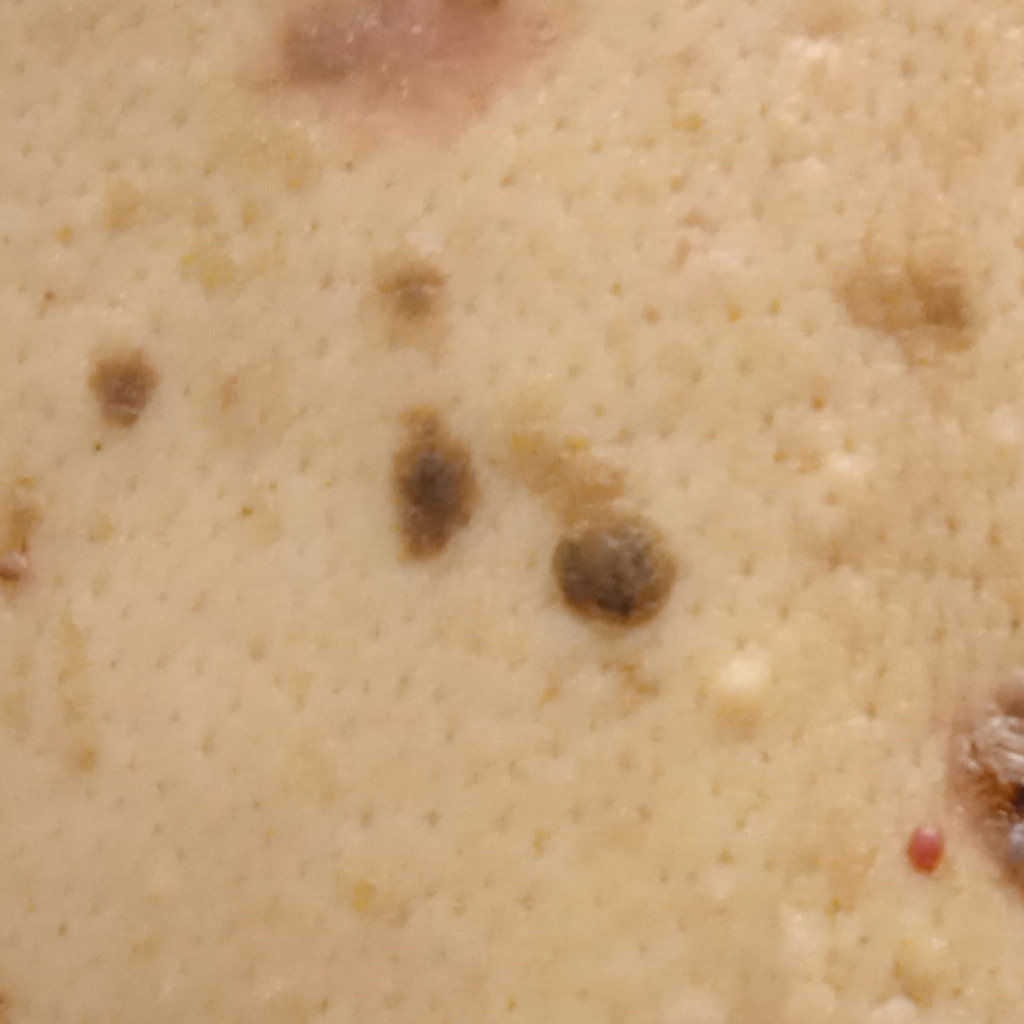The patient describes having a moderate number of moles.
Collected as part of a research study, without a referral diagnosis.
The patient says their skin tans without first burning.
A male subject 65 years old.
A clinical photograph showing a skin lesion.
The lesion measures approximately 10.3 mm.
Dermatologist review favored a seborrheic keratosis.